A dermatoscopic image of a skin lesion:
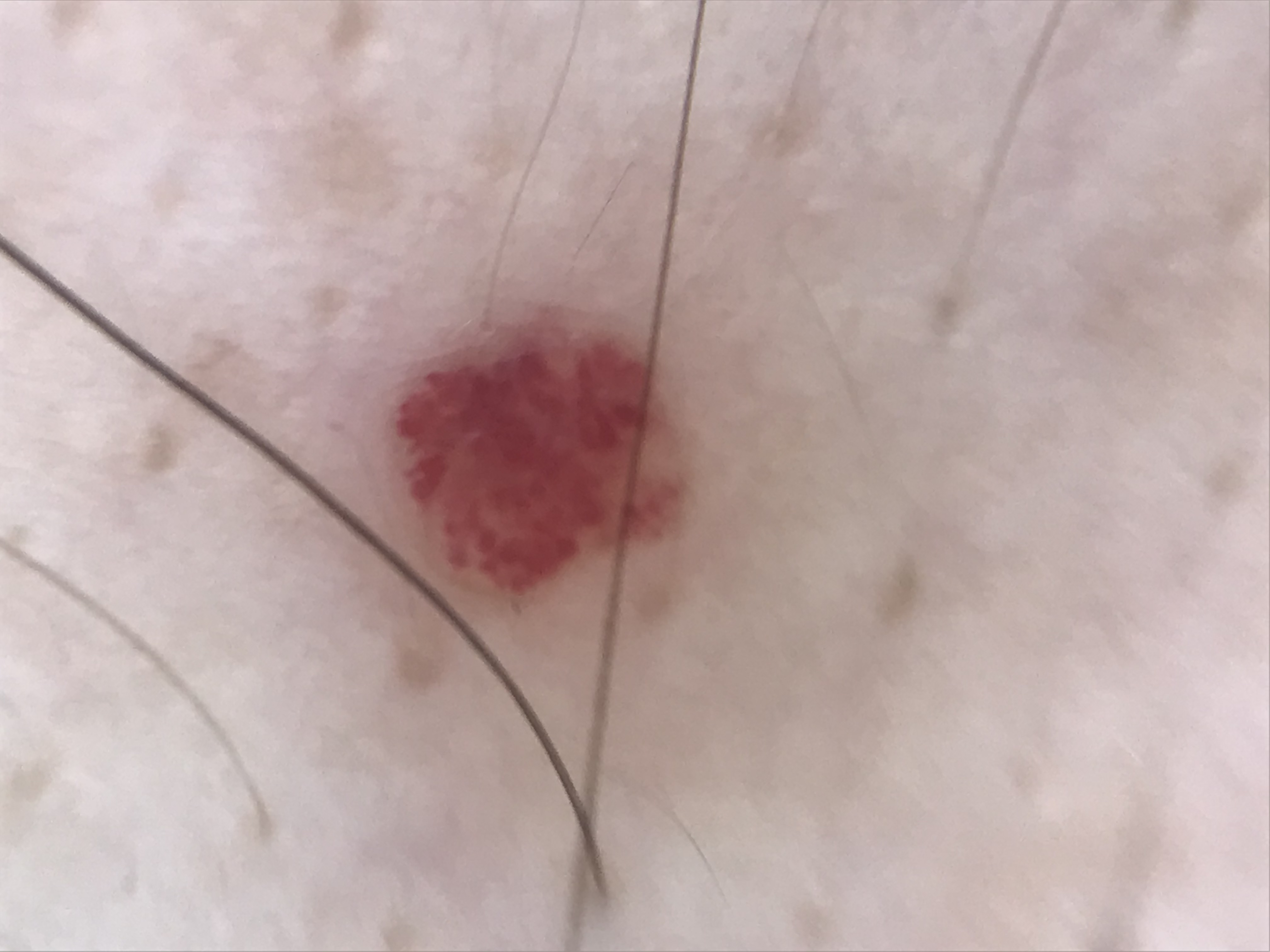Diagnosed as a hemangioma.